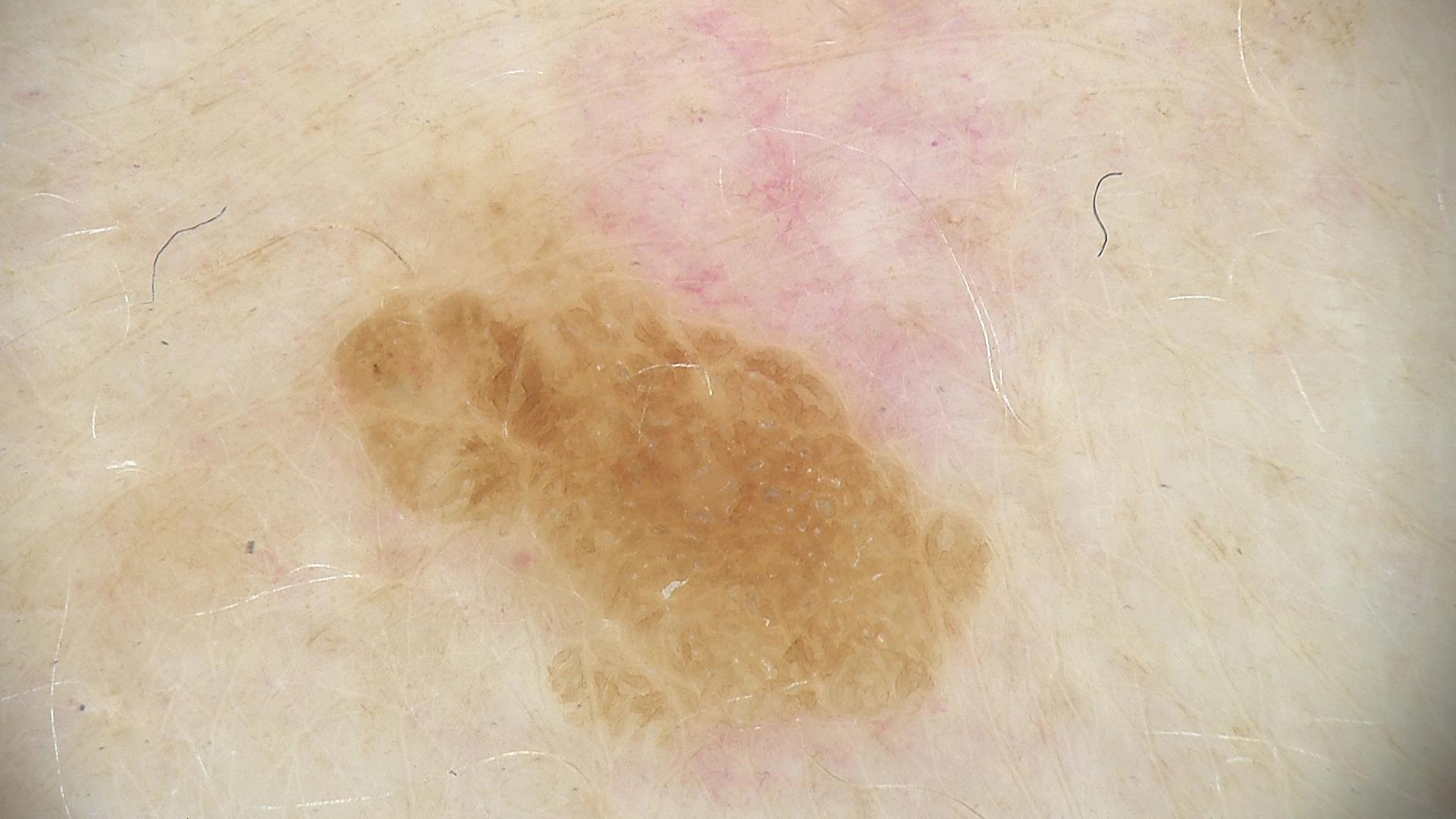A dermoscopic close-up of a skin lesion.
The architecture is that of a keratinocytic lesion.
Consistent with a seborrheic keratosis.